Dermoscopy of a skin lesion.
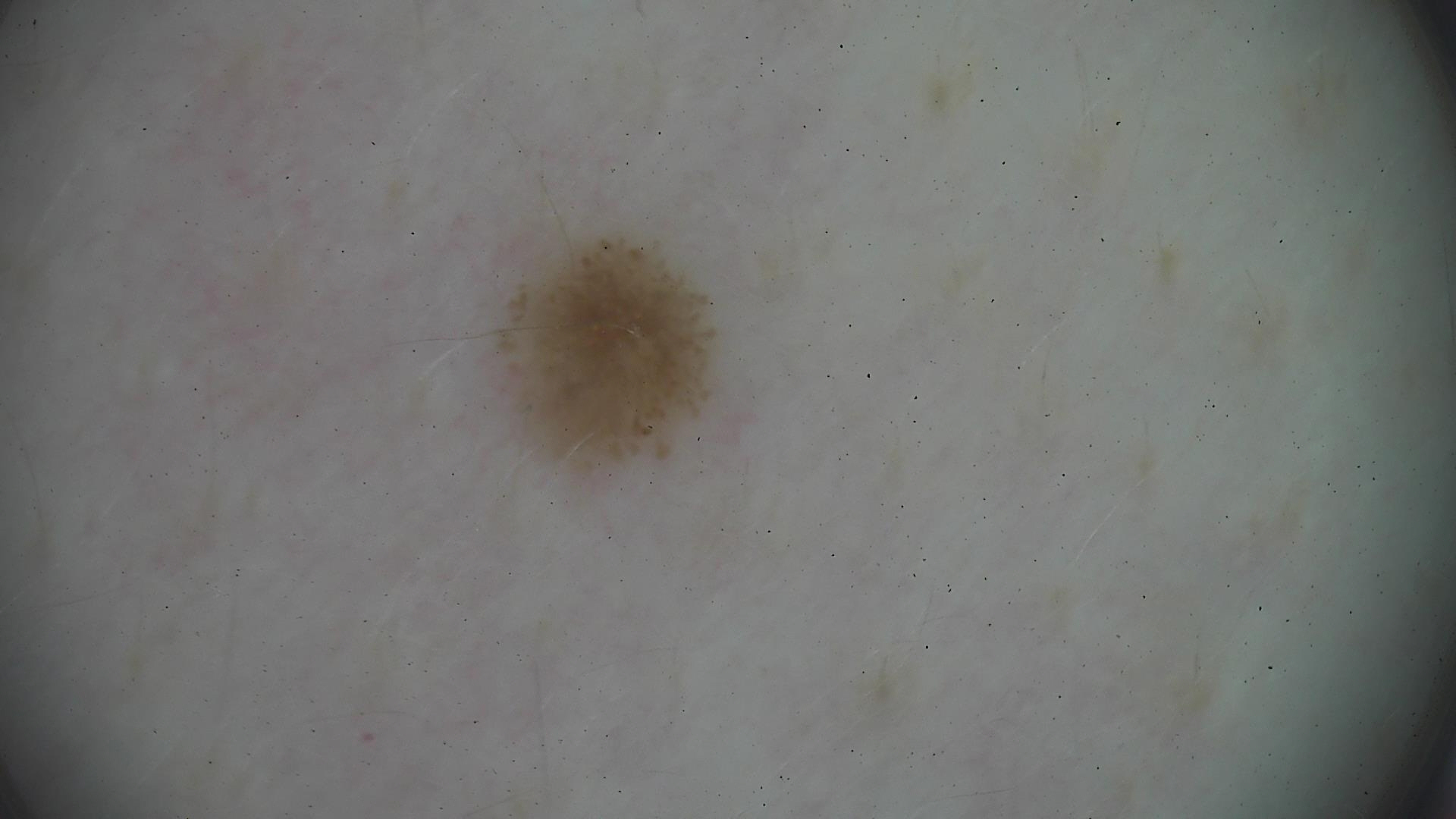class: dysplastic junctional nevus (expert consensus).